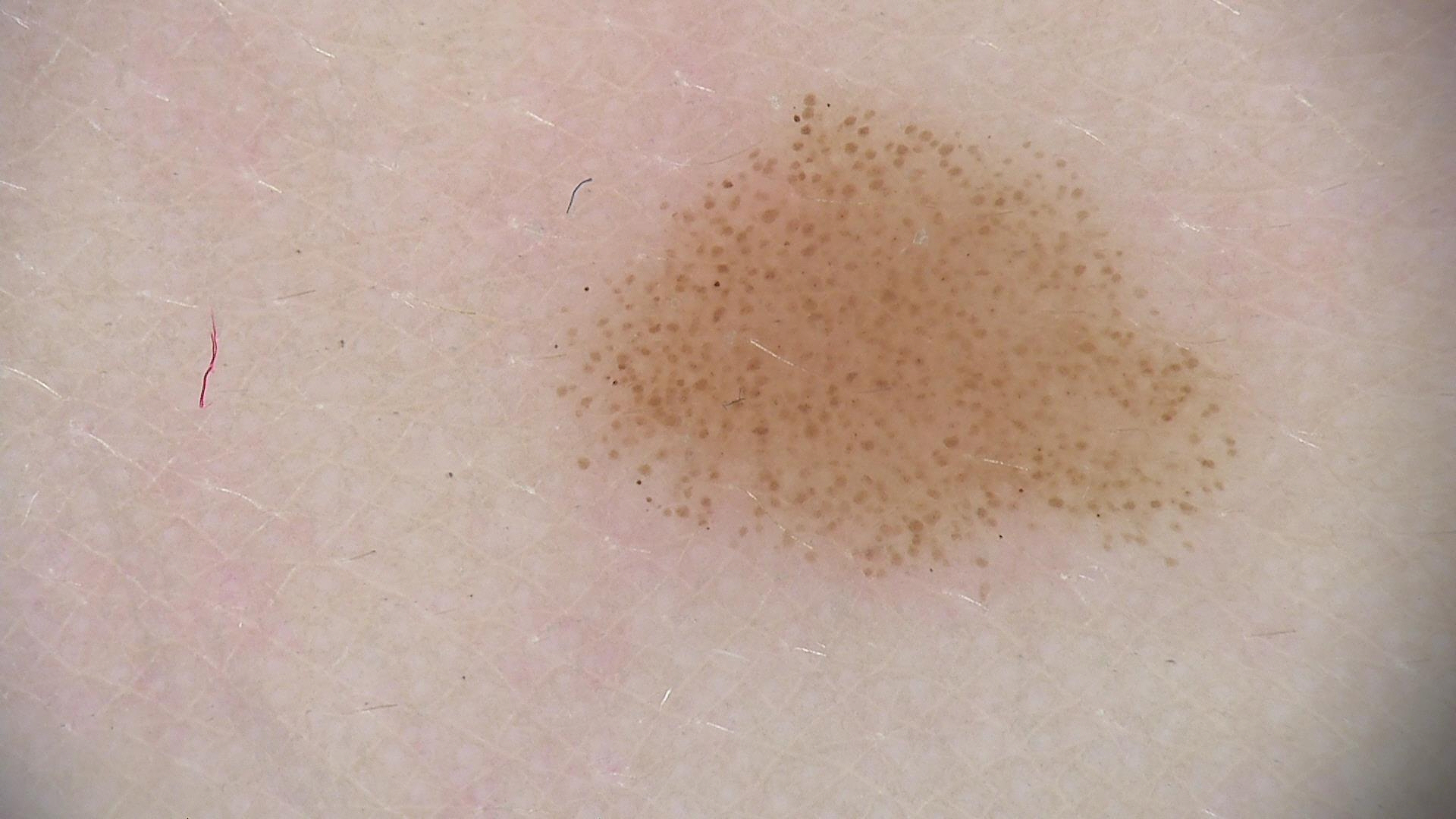Diagnosed as a dysplastic junctional nevus.